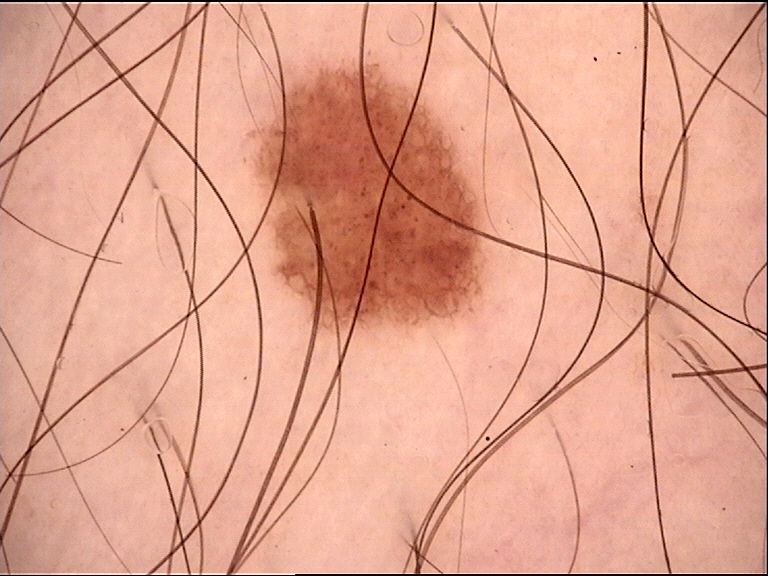The diagnosis was a dysplastic junctional nevus.